Located on the leg; this is a close-up image — 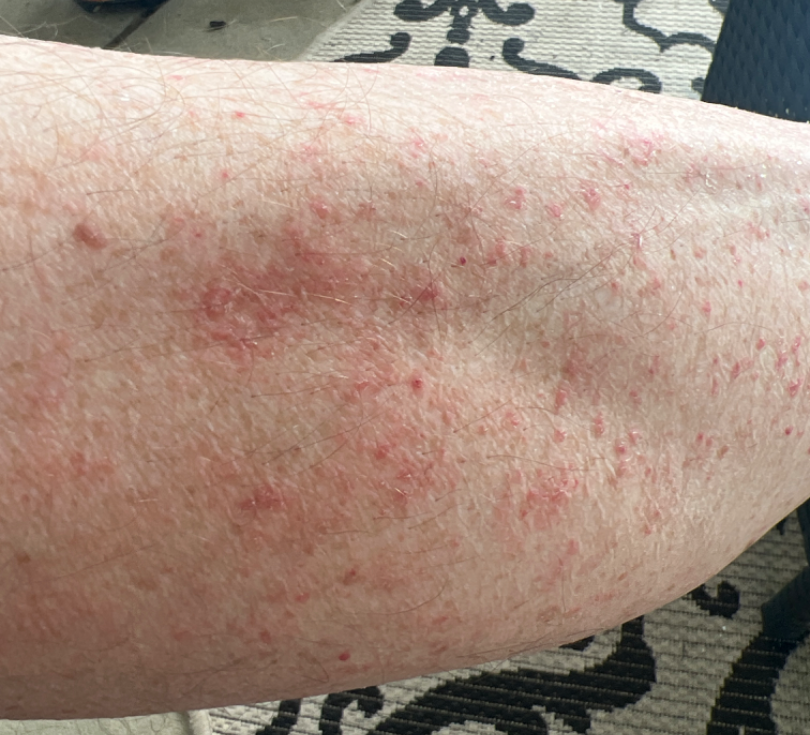Reviewed remotely by one dermatologist: most consistent with Acute dermatitis, NOS.